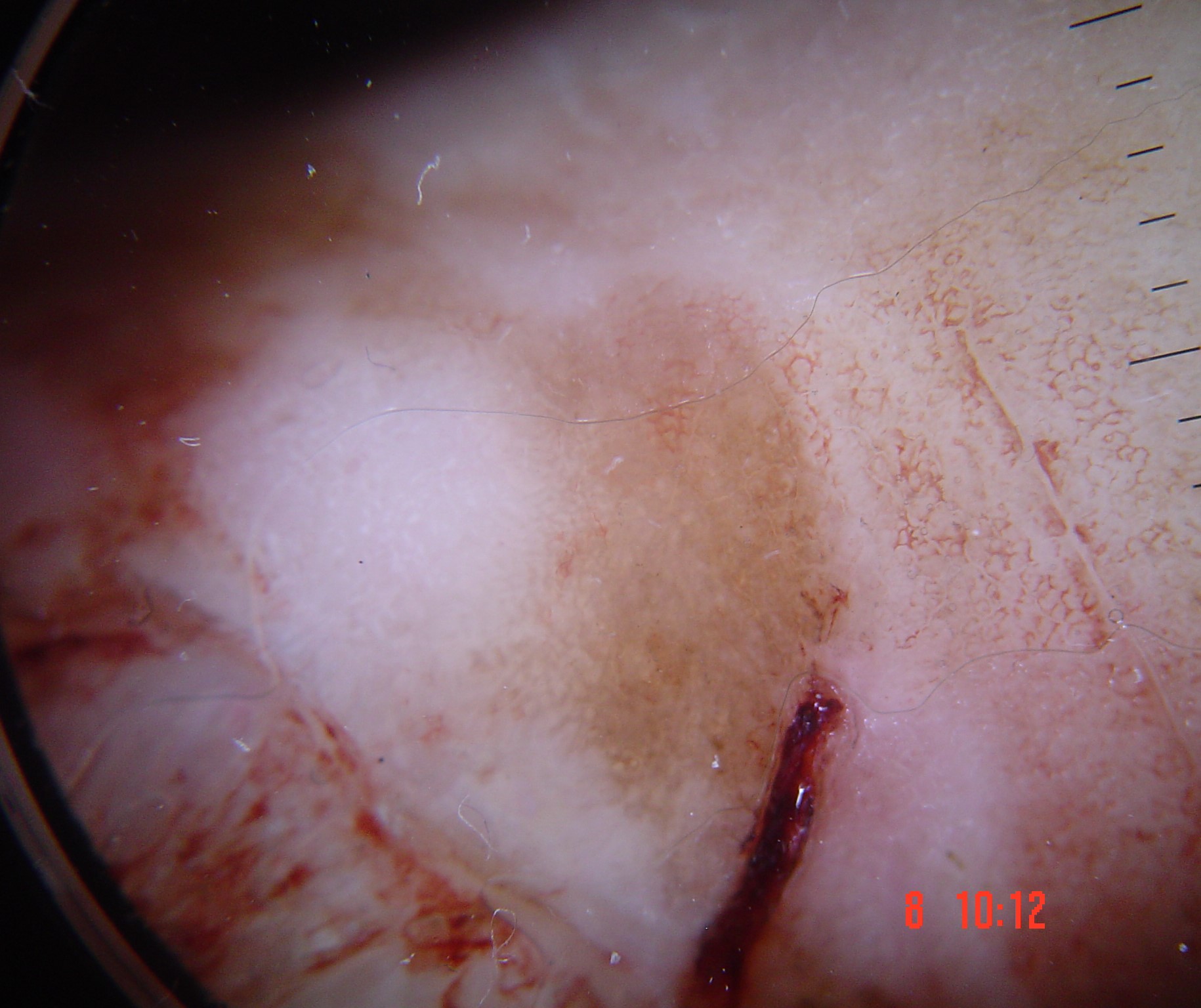Histopathology confirmed an acral nodular melanoma.